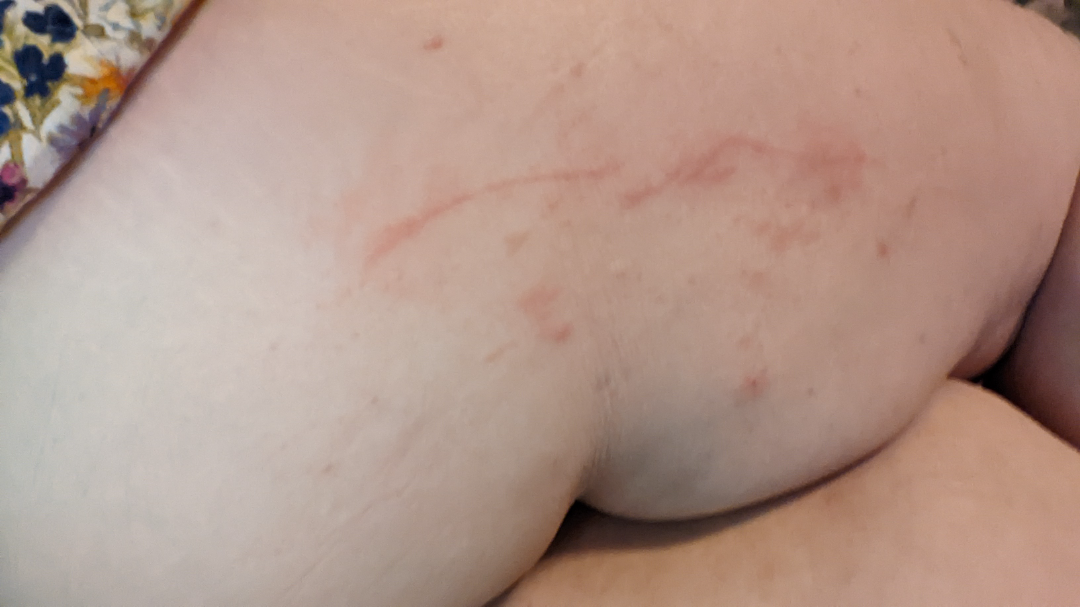The lesion involves the leg. This image was taken at a distance. Skin tone: Fitzpatrick skin type II; lay graders estimated 2 on the Monk Skin Tone. The contributor is female. The lesion is described as raised or bumpy. Self-categorized by the patient as a rash. Symptoms reported: itching. Present for less than one week. On remote dermatologist review: favoring Hypersensitivity; also raised was Eczema; with consideration of Allergic Contact Dermatitis; less probable is Inflicted skin lesions; less likely is Urticaria; lower on the differential is Flagellate erythema.